A dermoscopic image of a skin lesion:
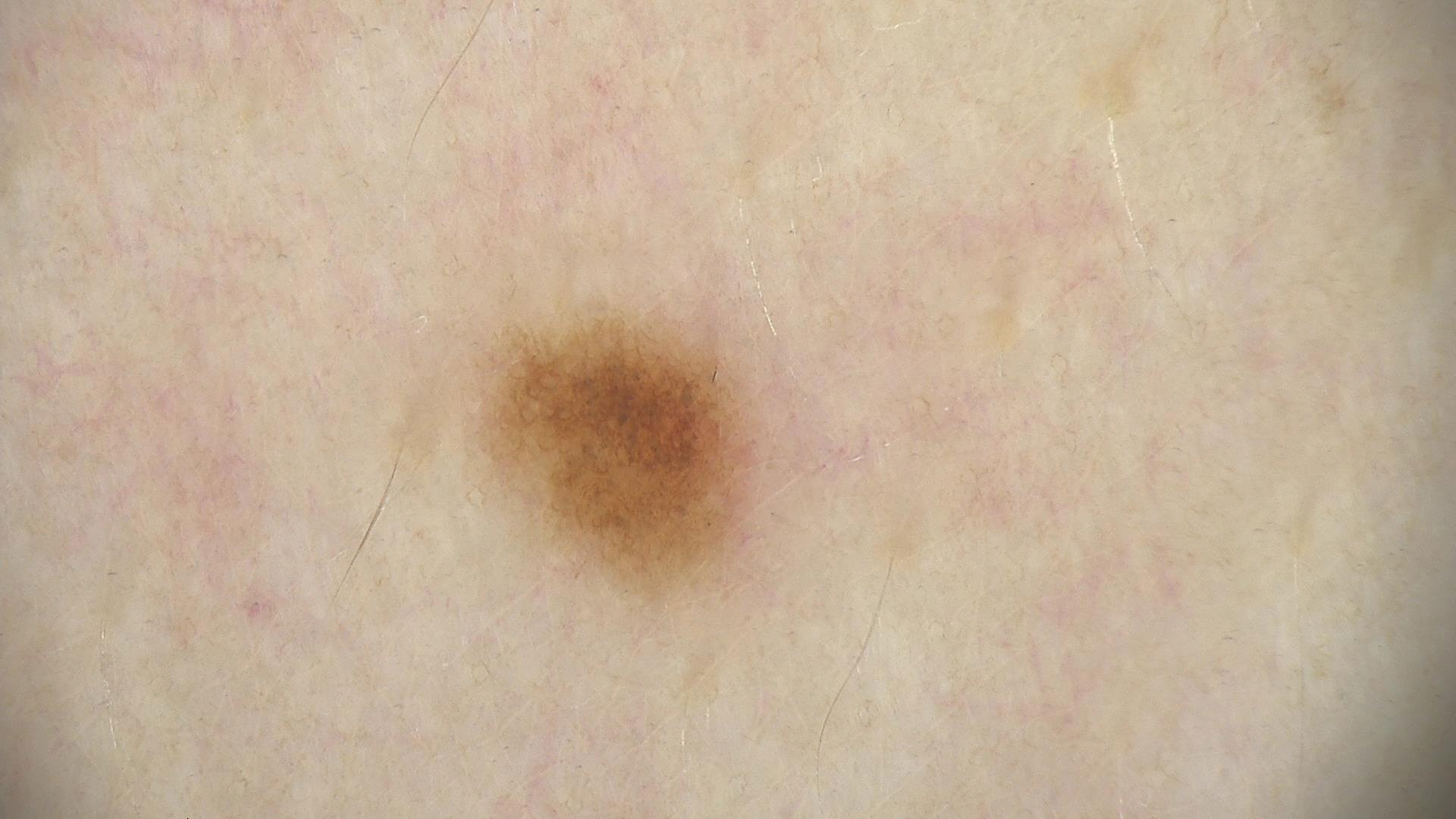Impression: Diagnosed as a dysplastic junctional nevus.